A dermoscopy image of a single skin lesion:
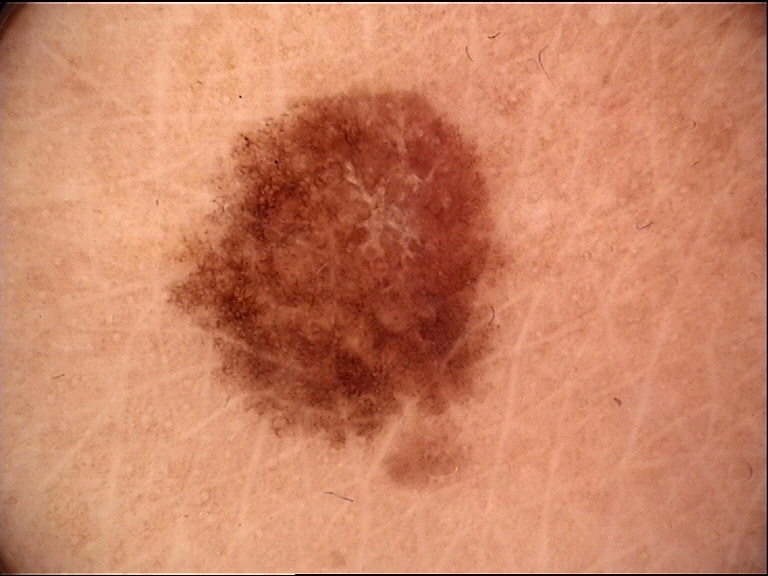The diagnostic label was a dysplastic junctional nevus.